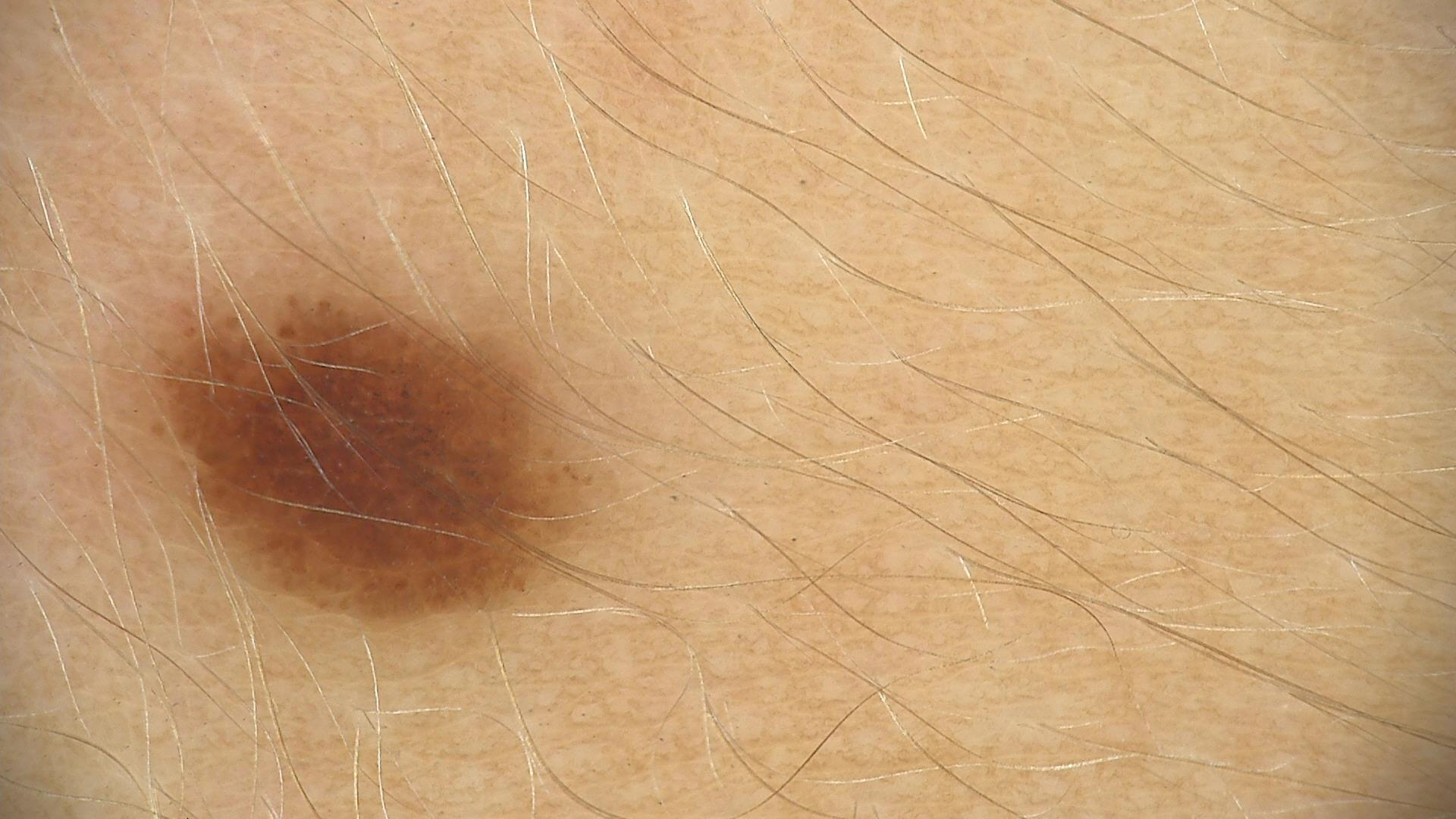{"image": "dermatoscopy", "diagnosis": {"name": "dysplastic junctional nevus", "code": "jd", "malignancy": "benign", "super_class": "melanocytic", "confirmation": "expert consensus"}}